The photo was captured at a distance.
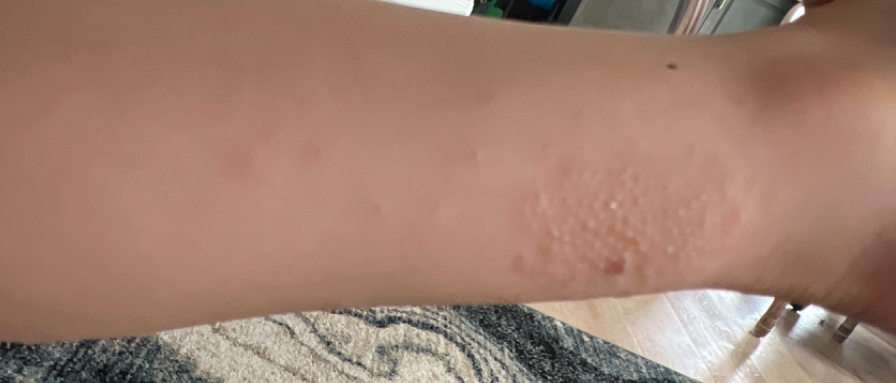{
  "assessment": "indeterminate from the photograph"
}